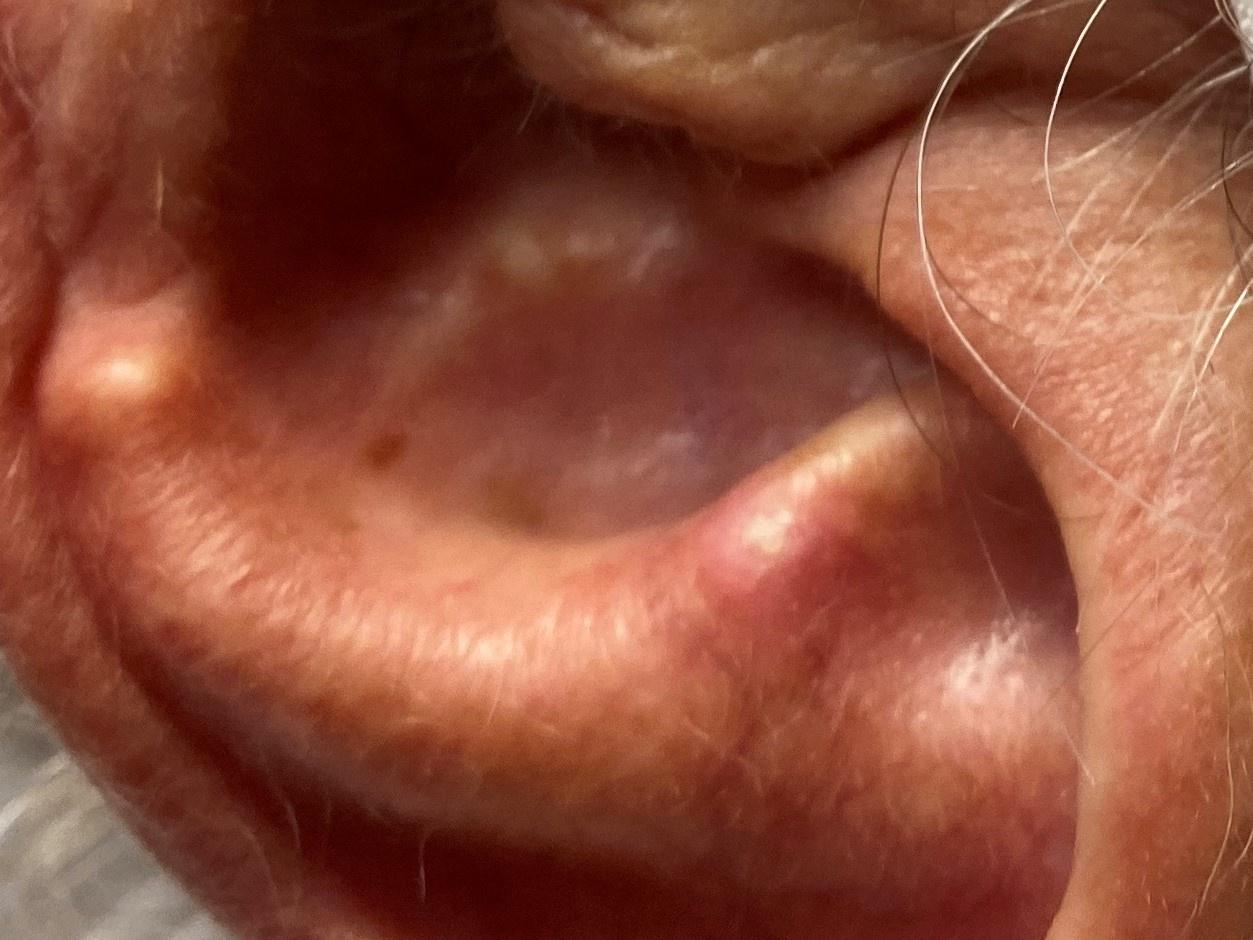{"skin_type": "III", "melanoma_history": {"personal_hx_melanoma": false, "family_hx_melanoma": false}, "patient": {"age_approx": 70, "sex": "male"}, "image": "clinical overview photograph", "lesion_location": {"region": "the head or neck"}, "diagnosis": {"name": "Solar or actinic keratosis", "malignancy": "indeterminate", "confirmation": "histopathology", "lineage": "epidermal"}}